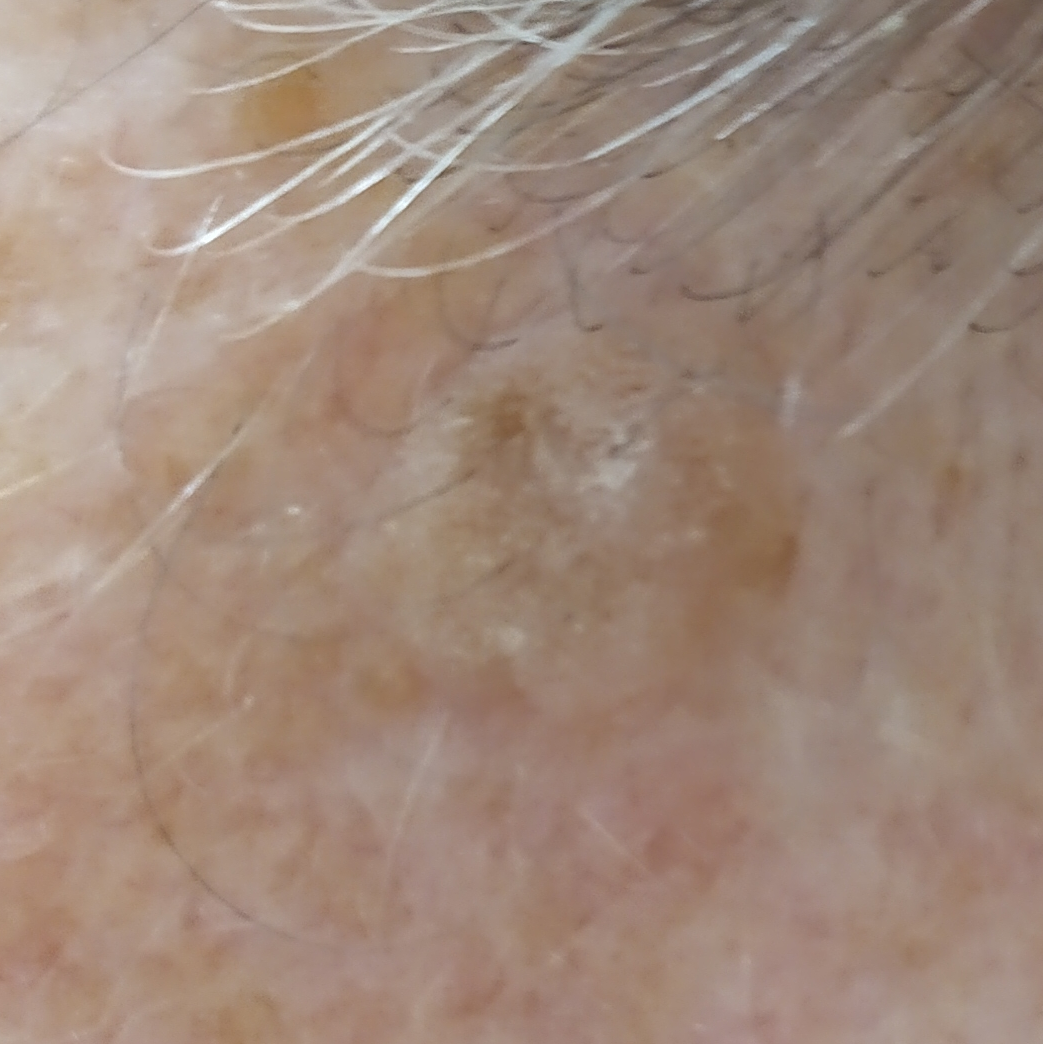Case:
• patient · in their 60s
• anatomic site · an ear
• assessment · actinic keratosis (clinical consensus)